The contributor reports the lesion is flat, close-up view, the affected area is the leg and arm, the patient described the issue as a rash — 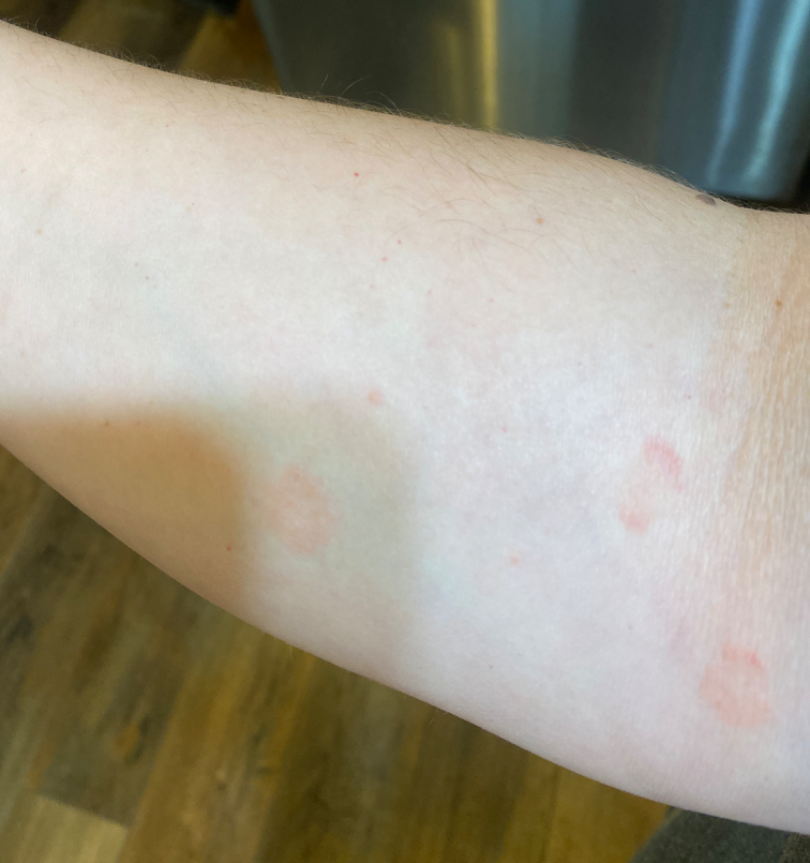<summary>
<assessment>indeterminate</assessment>
</summary>